Dermoscopy of a skin lesion:
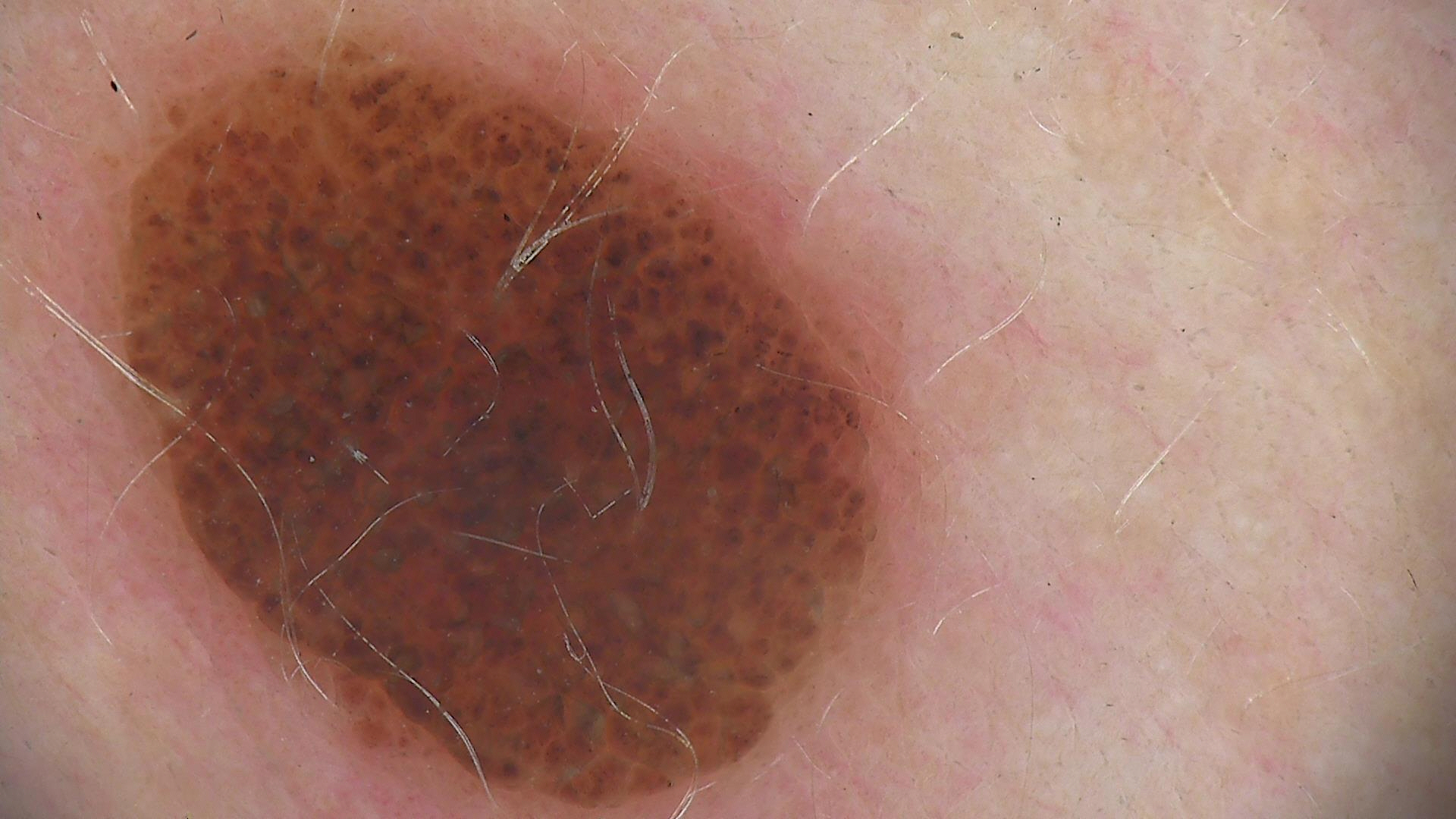Findings:
The architecture is that of a banal lesion.
Conclusion:
The diagnostic label was a compound nevus.